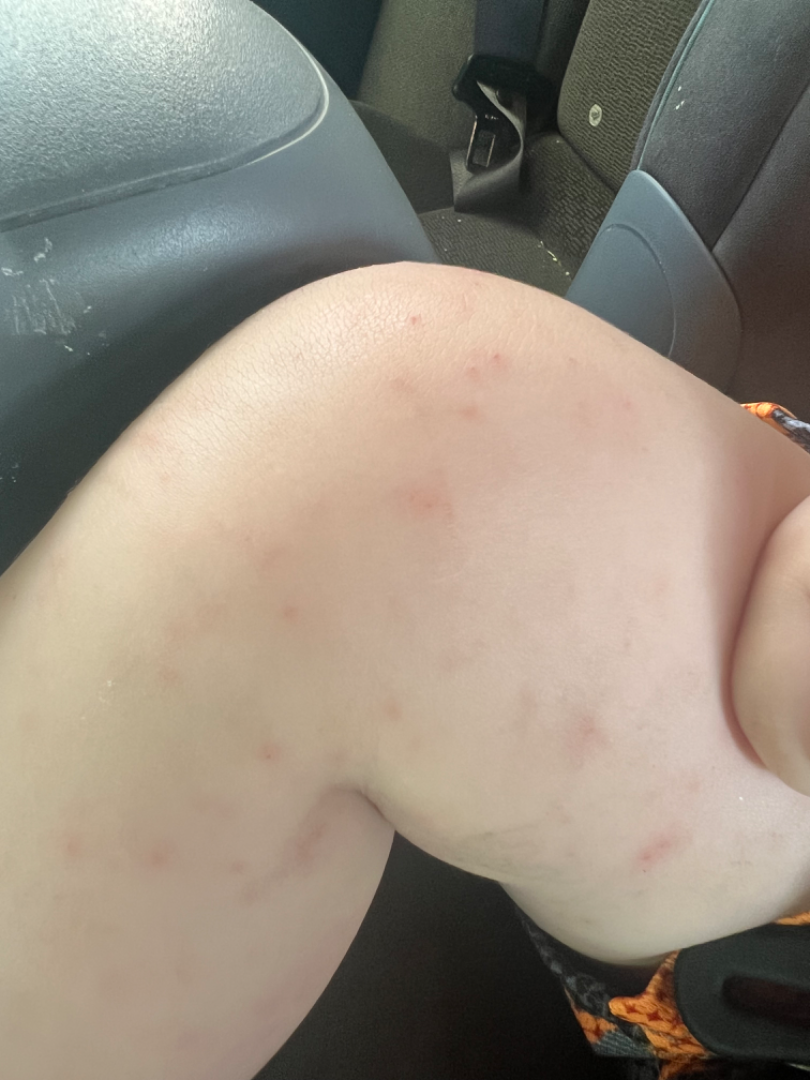assessment: indeterminate
shot_type: close-up
skin_tone:
  fitzpatrick: III